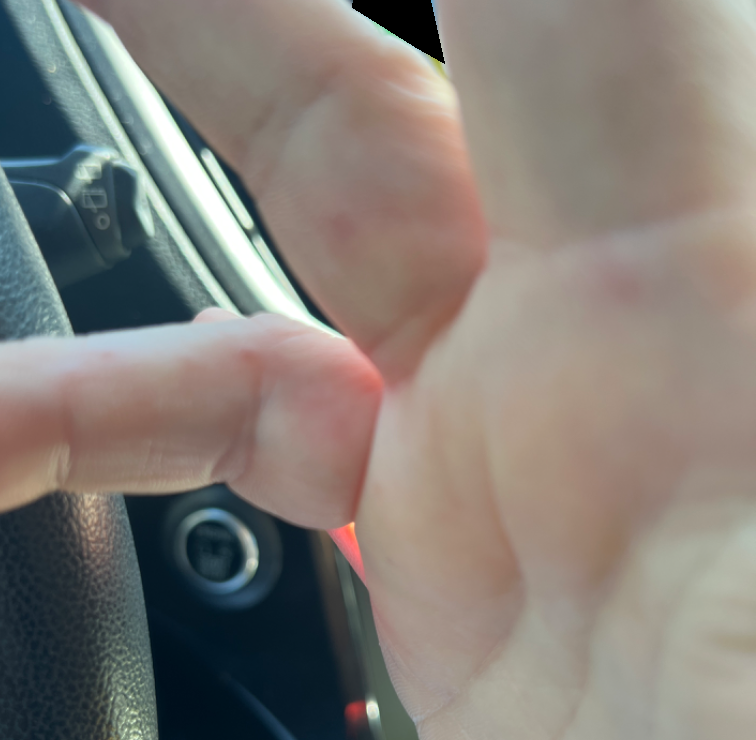Q: What was the assessment?
A: could not be assessed